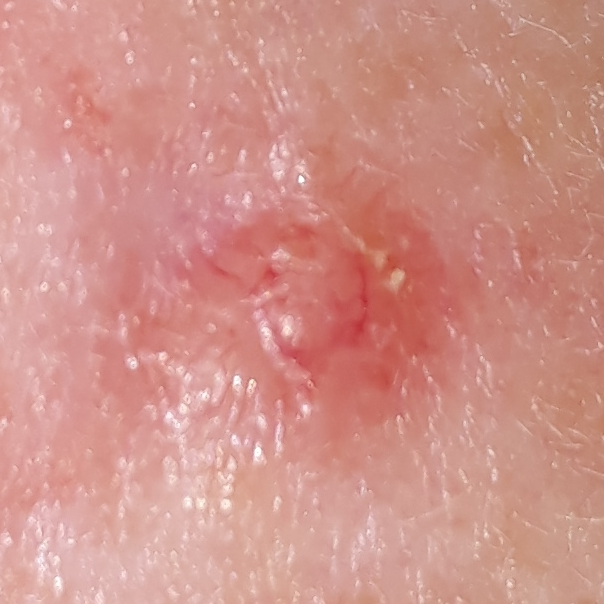Q: What did the workup show?
A: basal cell carcinoma (biopsy-proven)